A clinical photograph showing a skin lesion. A patient 41 years of age: 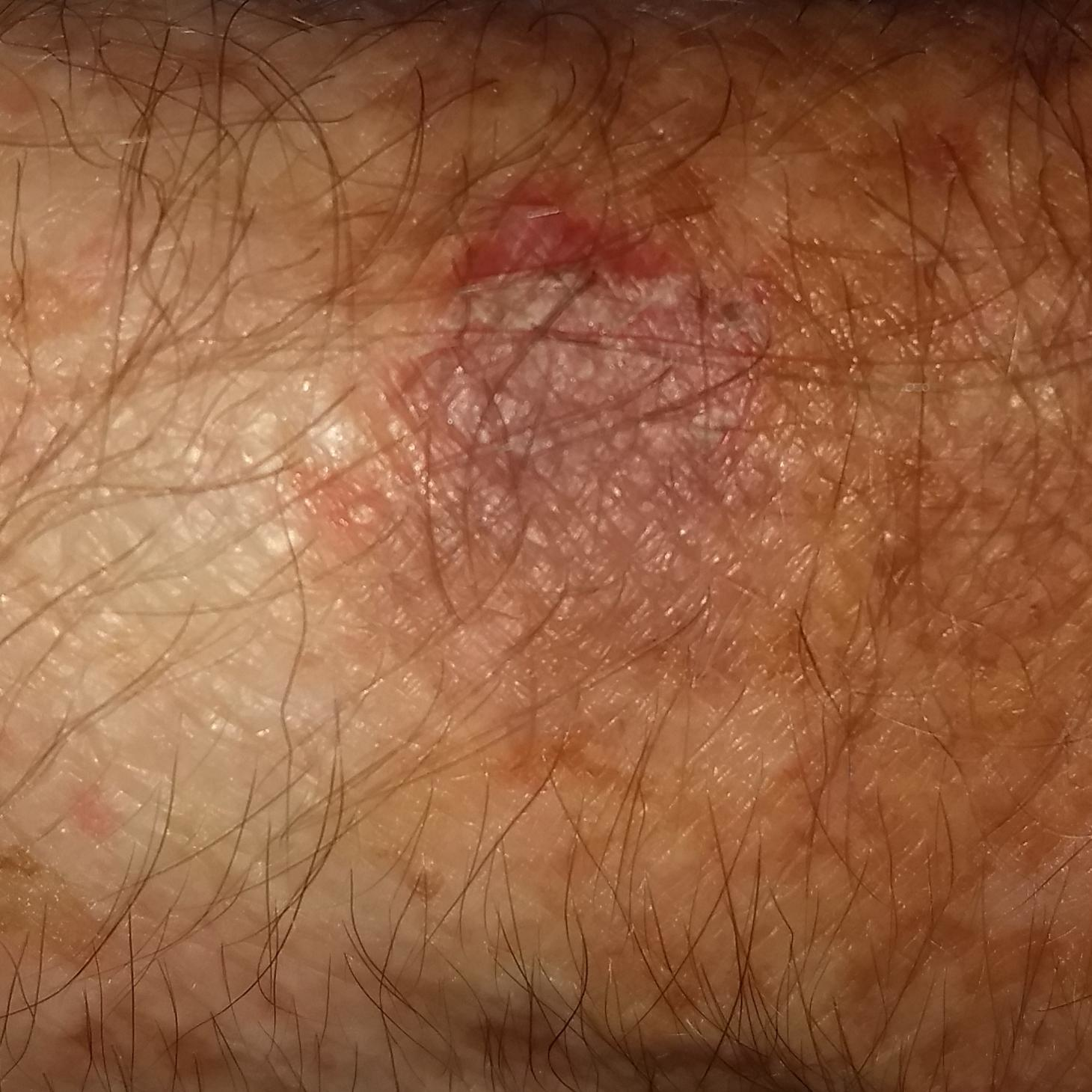The lesion is located on a forearm.
By the patient's account, the lesion itches.
Consistent with a premalignant lesion — an actinic keratosis.